A dermoscopy image of a single skin lesion: 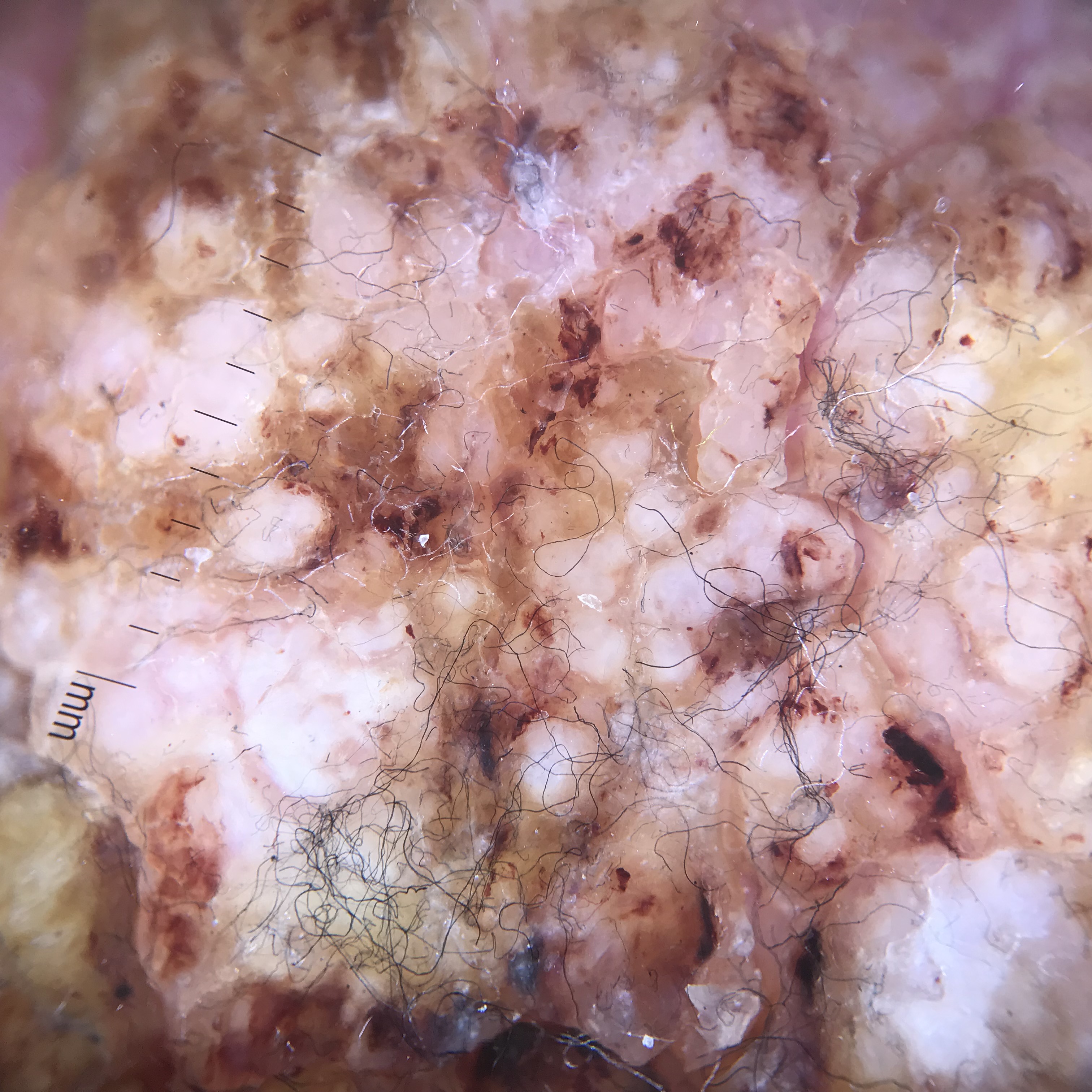Case:
* diagnosis — squamous cell carcinoma (biopsy-proven)